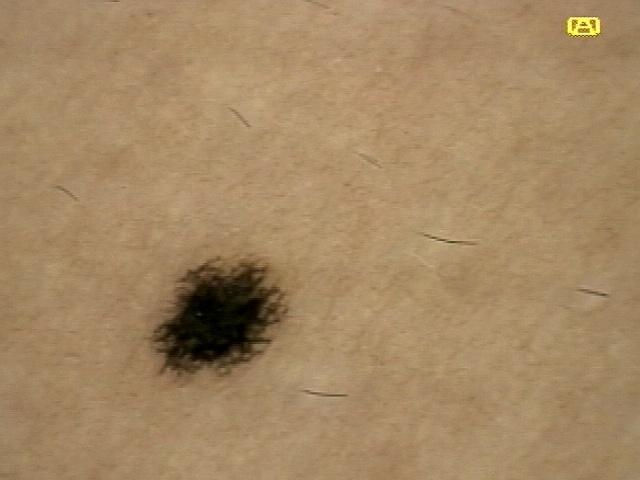A female patient aged 28 to 32.
A dermoscopic close-up of a skin lesion.
The lesion is located on the trunk, specifically the anterior trunk.
Consistent with a lesion of melanocytic lineage — a nevus.